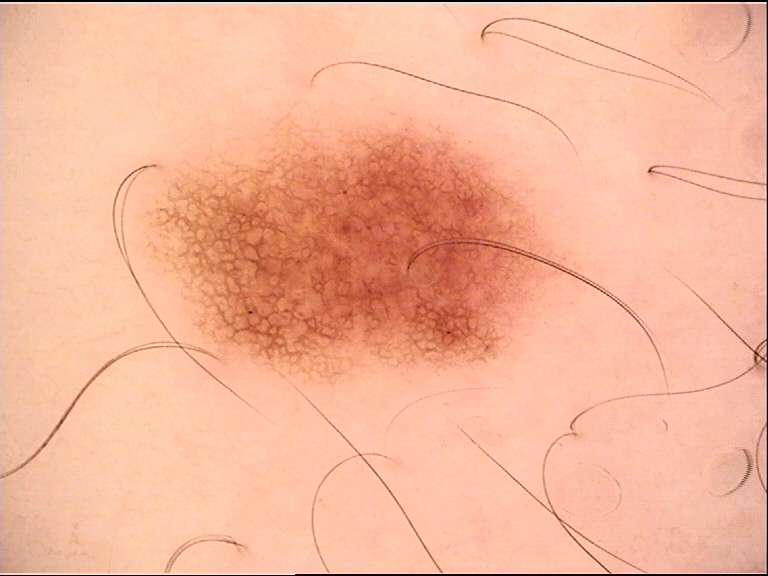Summary:
A dermoscopy image of a single skin lesion.
Conclusion:
Classified as a benign lesion — a dysplastic junctional nevus.